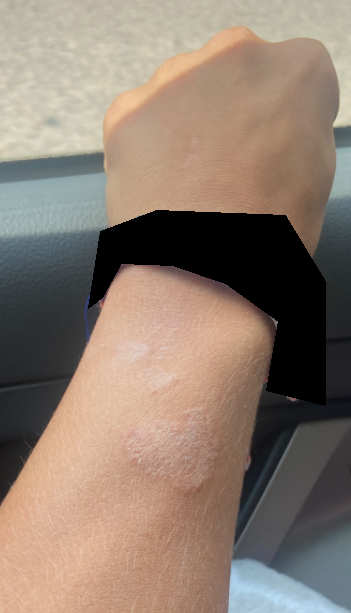The photo was captured at a distance. Located on the arm. Male contributor, age 18–29. On teledermatology review: Eczema and Psoriasis were each considered, in no particular order.